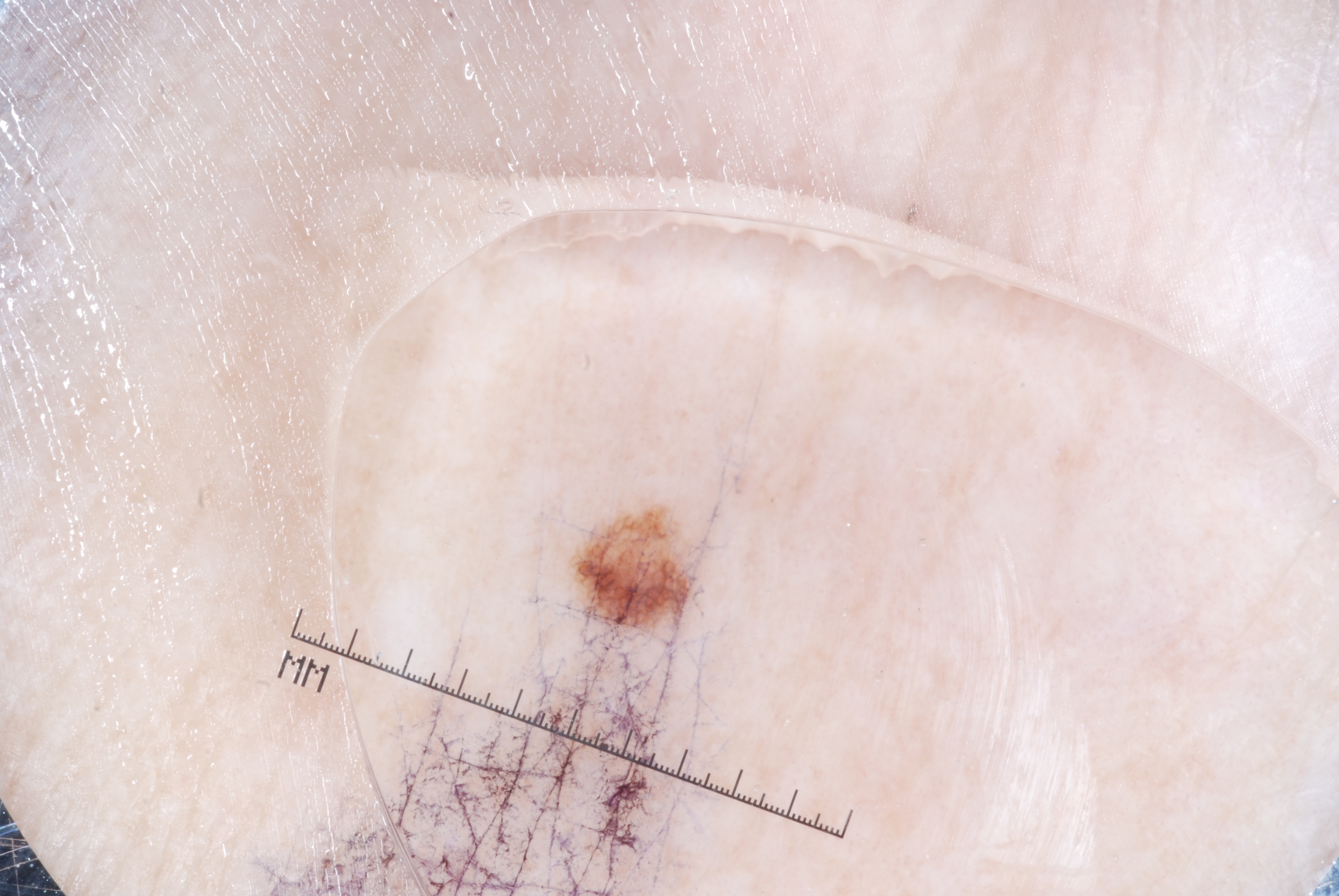A dermoscopic close-up of a skin lesion.
The subject is a female aged around 60.
Dermoscopy demonstrates pigment network; no negative network, streaks, or milia-like cysts.
As (left, top, right, bottom), the visible lesion spans <box>569, 505, 695, 637</box>.
The lesion takes up about 1% of the image.
Expert review diagnosed this as a melanocytic nevus, a benign skin lesion.